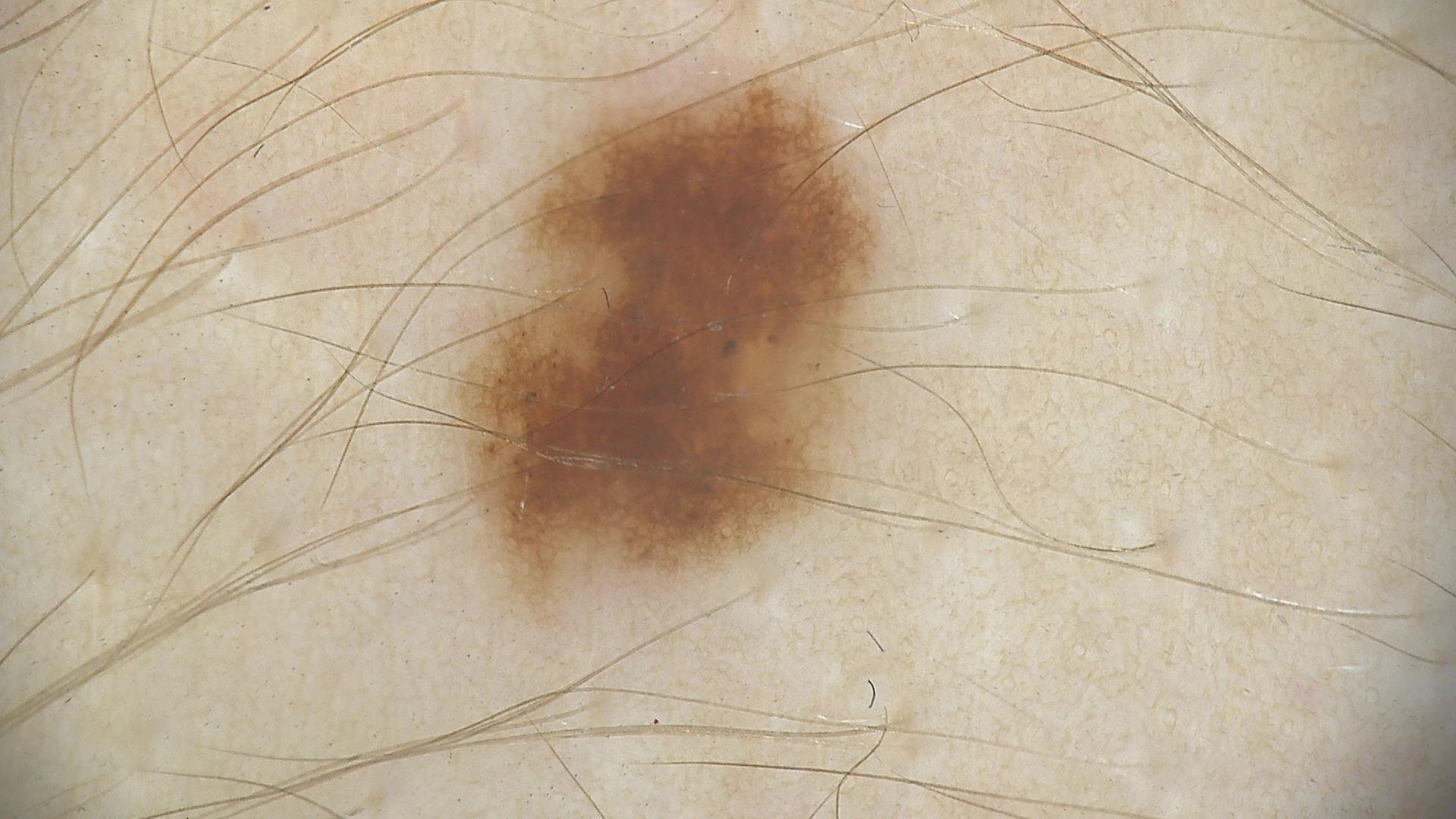class = dysplastic junctional nevus (expert consensus)